A dermatoscopic image of a skin lesion. The patient says their skin reddens with sun exposure. A male patient age 62. Acquired for a research image collection, with no referral diagnosis. Few moles overall by the patient's own estimate: 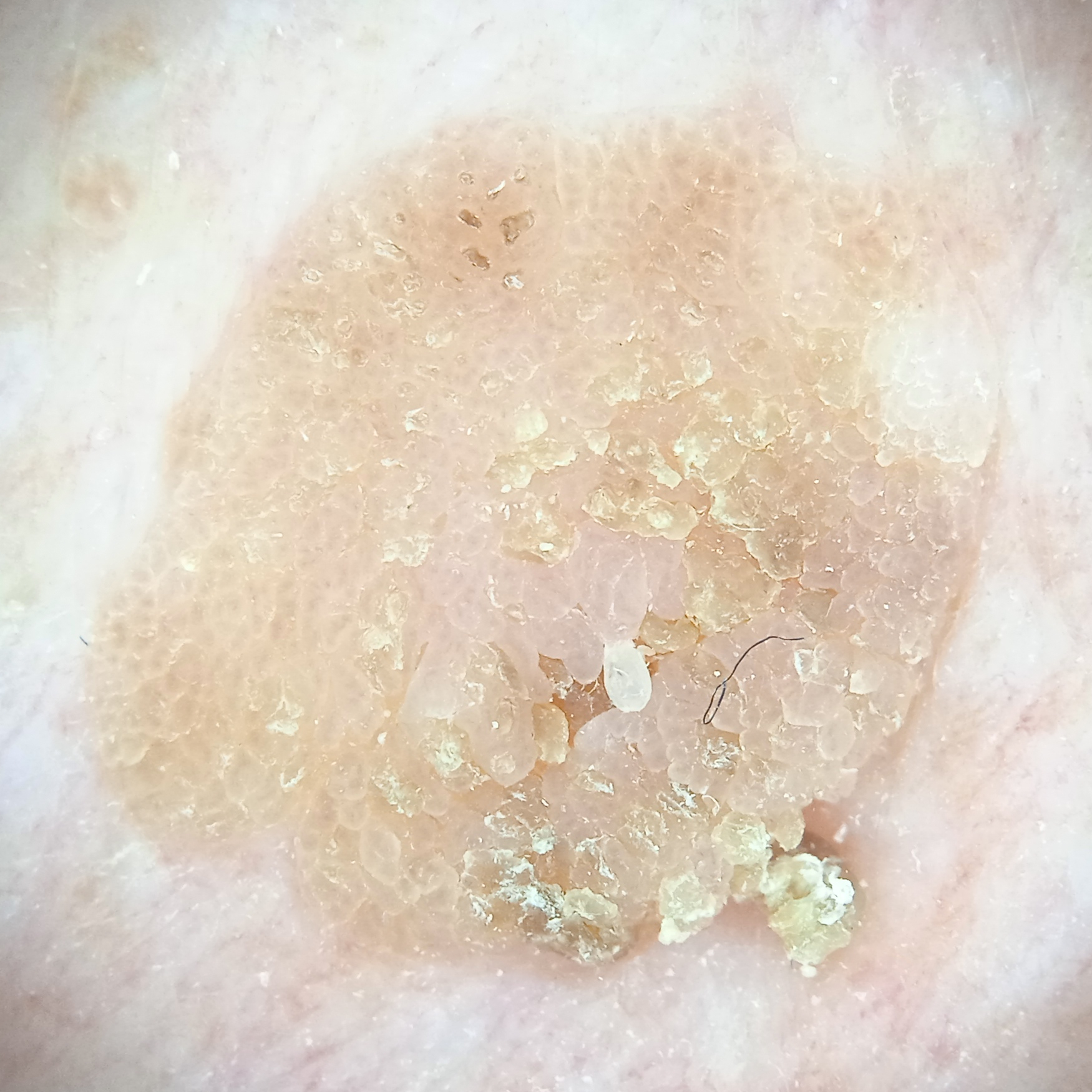Q: Lesion size?
A: 11.3 mm
Q: What was the diagnosis?
A: seborrheic keratosis (dermatologist consensus)